A male patient in their early 50s; by history, alcohol use, pesticide exposure, and prior malignancy (patient or family); skin type II; a clinical photograph of a skin lesion.
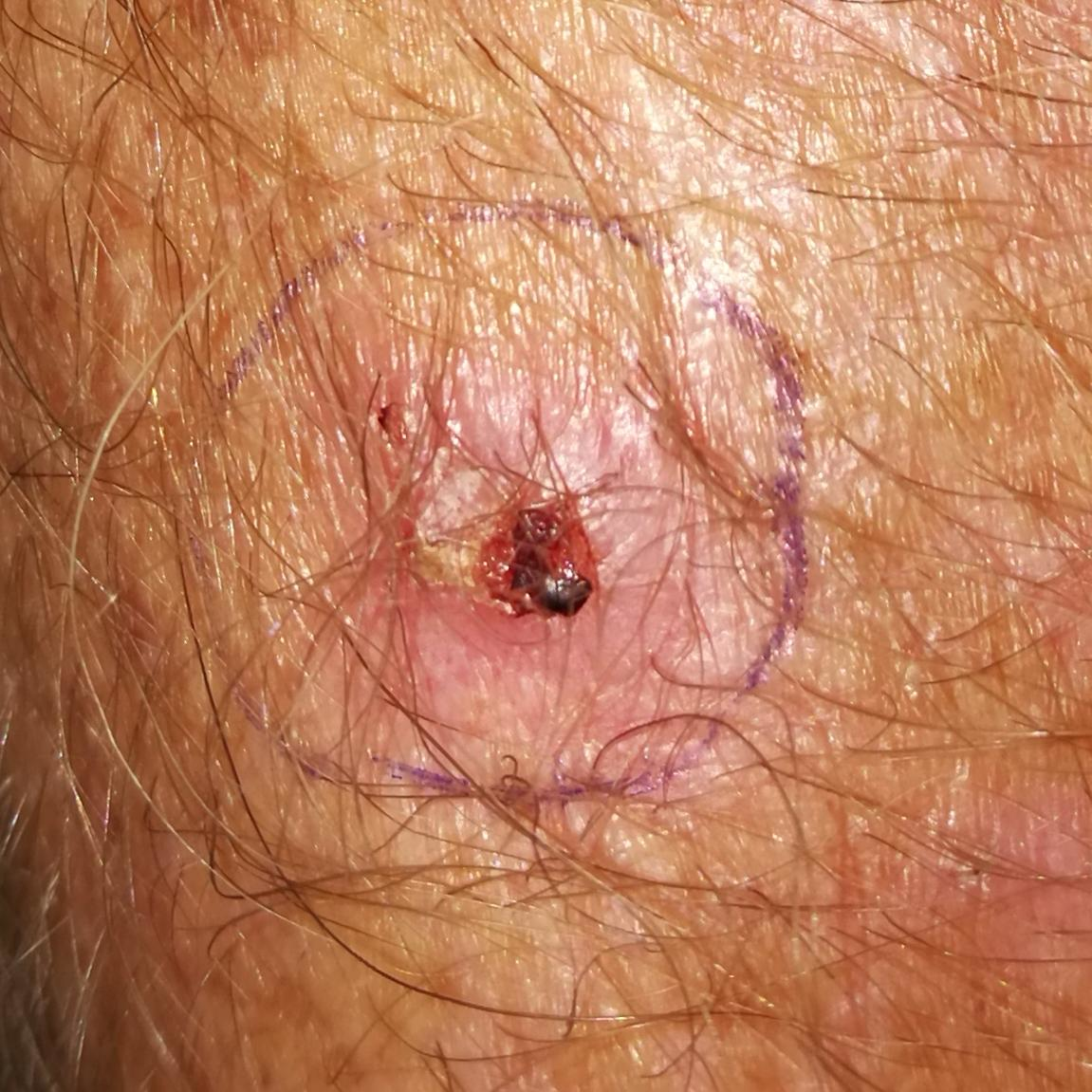anatomic site=the back; lesion diameter=12 × 6 mm; reported symptoms=elevation, bleeding, pain, itching; diagnosis=basal cell carcinoma (biopsy-proven).